By self-report, a history of sunbed use. The patient says their skin tans without first burning. The patient describes having a moderate number of moles. A female subject aged 47 — 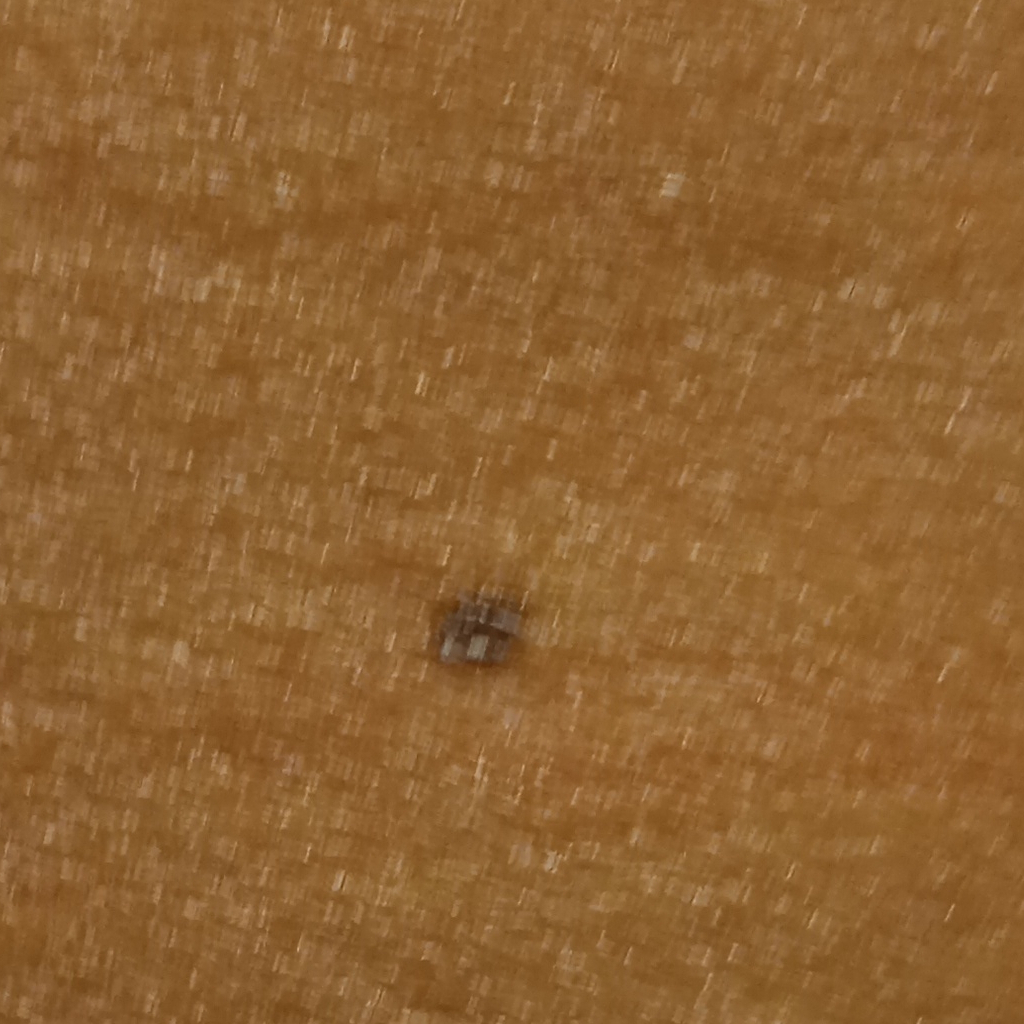{
  "lesion_location": "an arm",
  "lesion_size": {
    "diameter_mm": 3.3
  },
  "diagnosis": {
    "name": "melanocytic nevus",
    "malignancy": "benign"
  }
}